A female subject 35 years of age. The patient says their skin reddens painfully with sun exposure. The patient describes having a moderate number of moles. A dermoscopy image of a skin lesion. Collected as part of a research study, without a referral diagnosis — 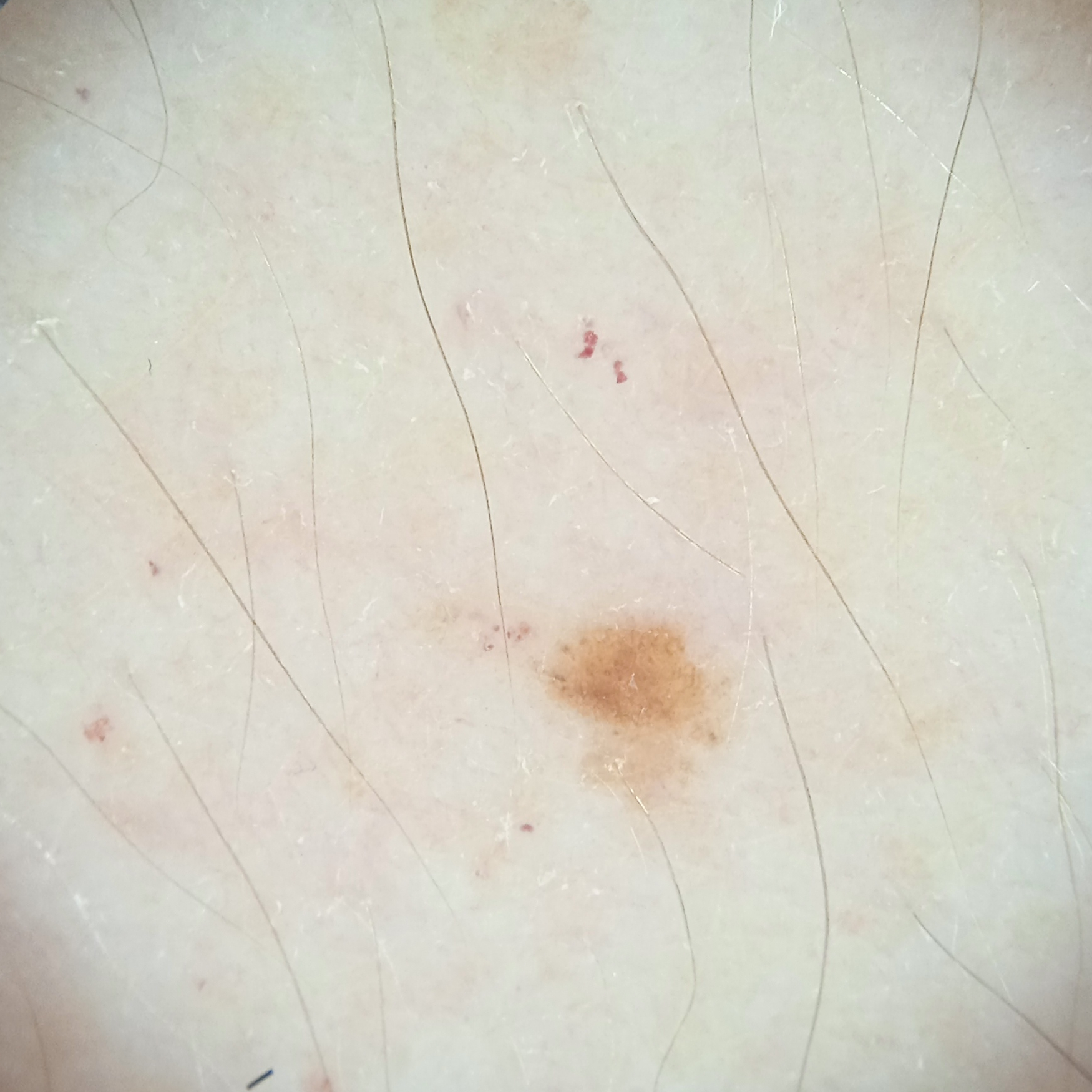site: an arm; size: 2.1 mm; assessment: melanocytic nevus (dermatologist consensus).